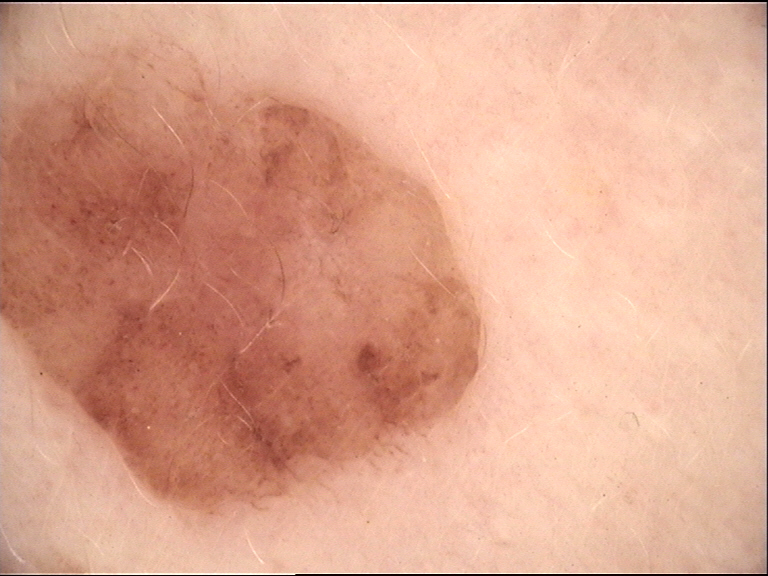Impression: The diagnostic label was a dermal nevus.